A male subject, aged 53 to 57; this is a dermoscopic photograph of a skin lesion — 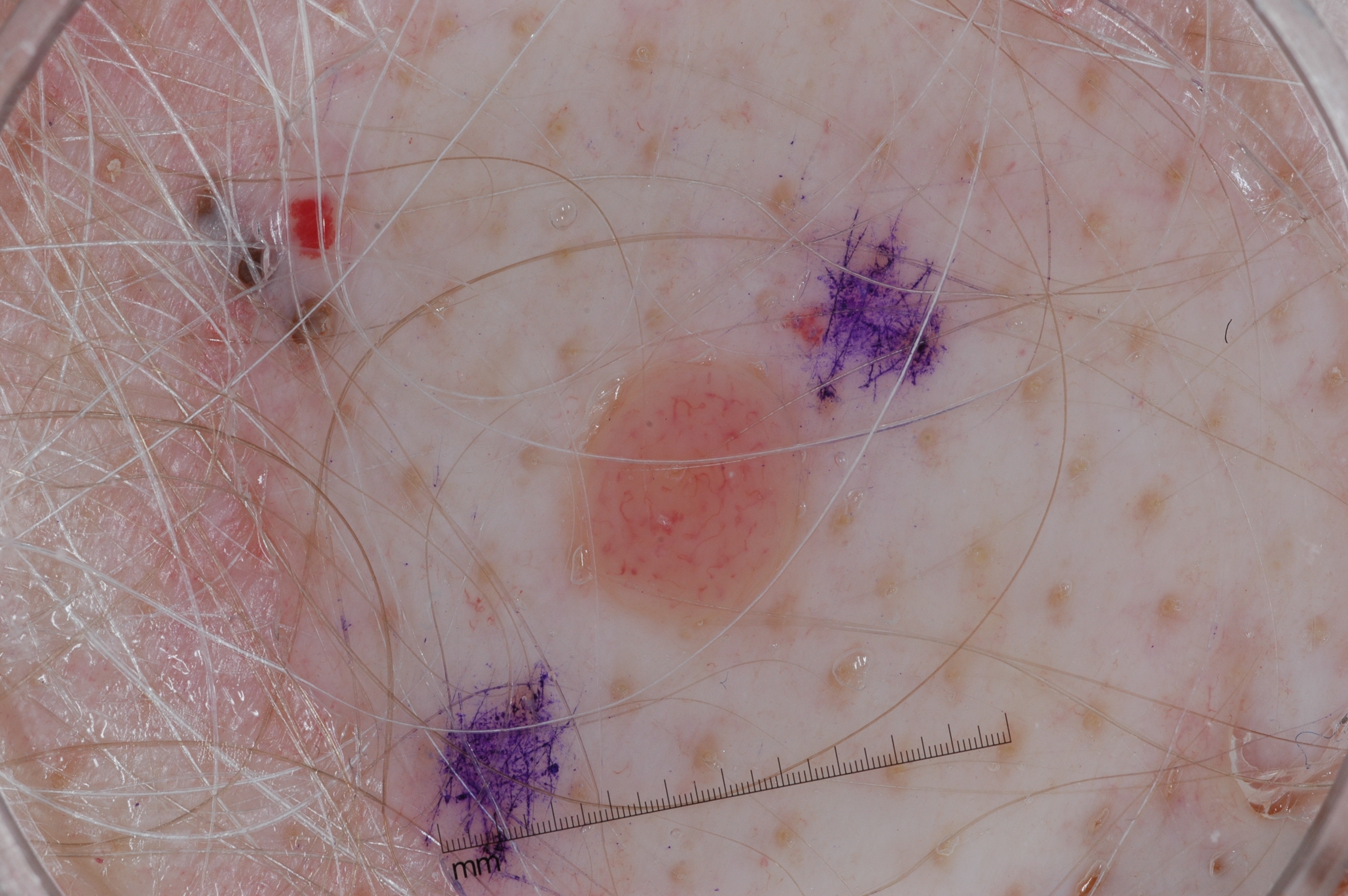extent = small
lesion bbox = 562, 349, 803, 638
dermoscopic features = milia-like cysts; absent: streaks, pigment network, and negative network
diagnostic label = a melanocytic nevus